A dermoscopy image of a single skin lesion:
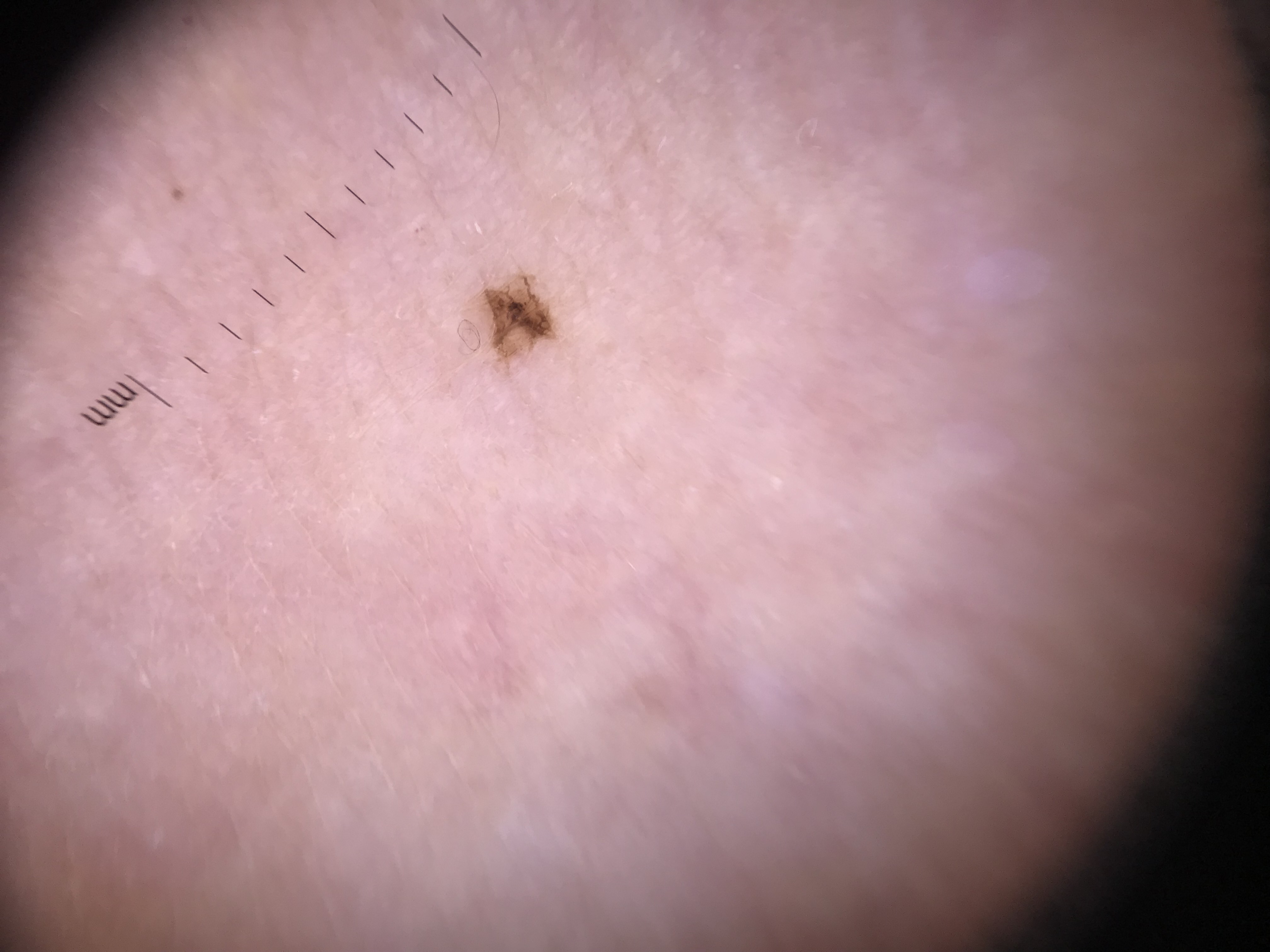Diagnosed as a benign lesion — an acral dysplastic junctional nevus.